The patient was assessed as Fitzpatrick skin type II; a male patient aged 43 to 47; per the chart, a first-degree relative with melanoma and a previous melanoma; a dermoscopic close-up of a skin lesion — 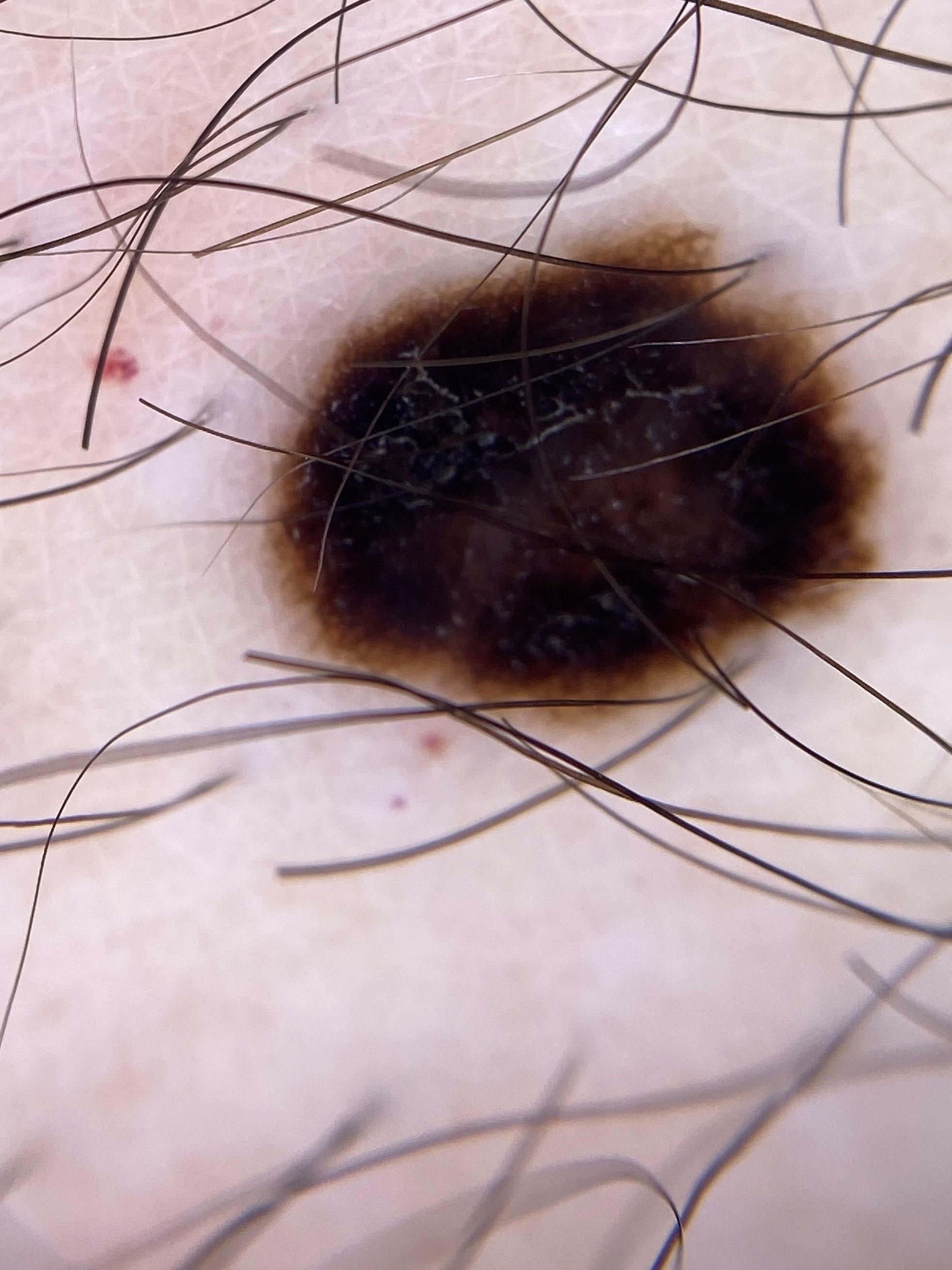Notes:
* body site · the trunk, specifically the anterior trunk
* pathology · Melanoma (biopsy-proven)